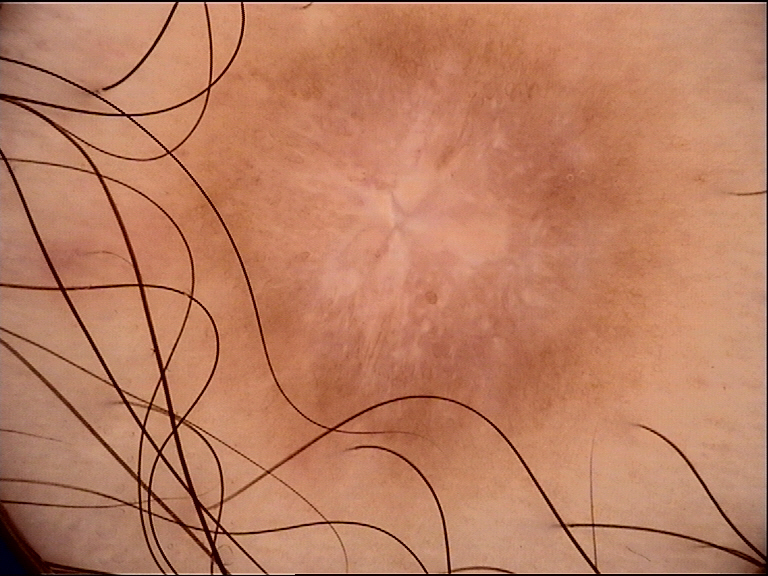A skin lesion imaged with a dermatoscope. Classified as a benign, fibro-histiocytic lesion — a dermatofibroma.